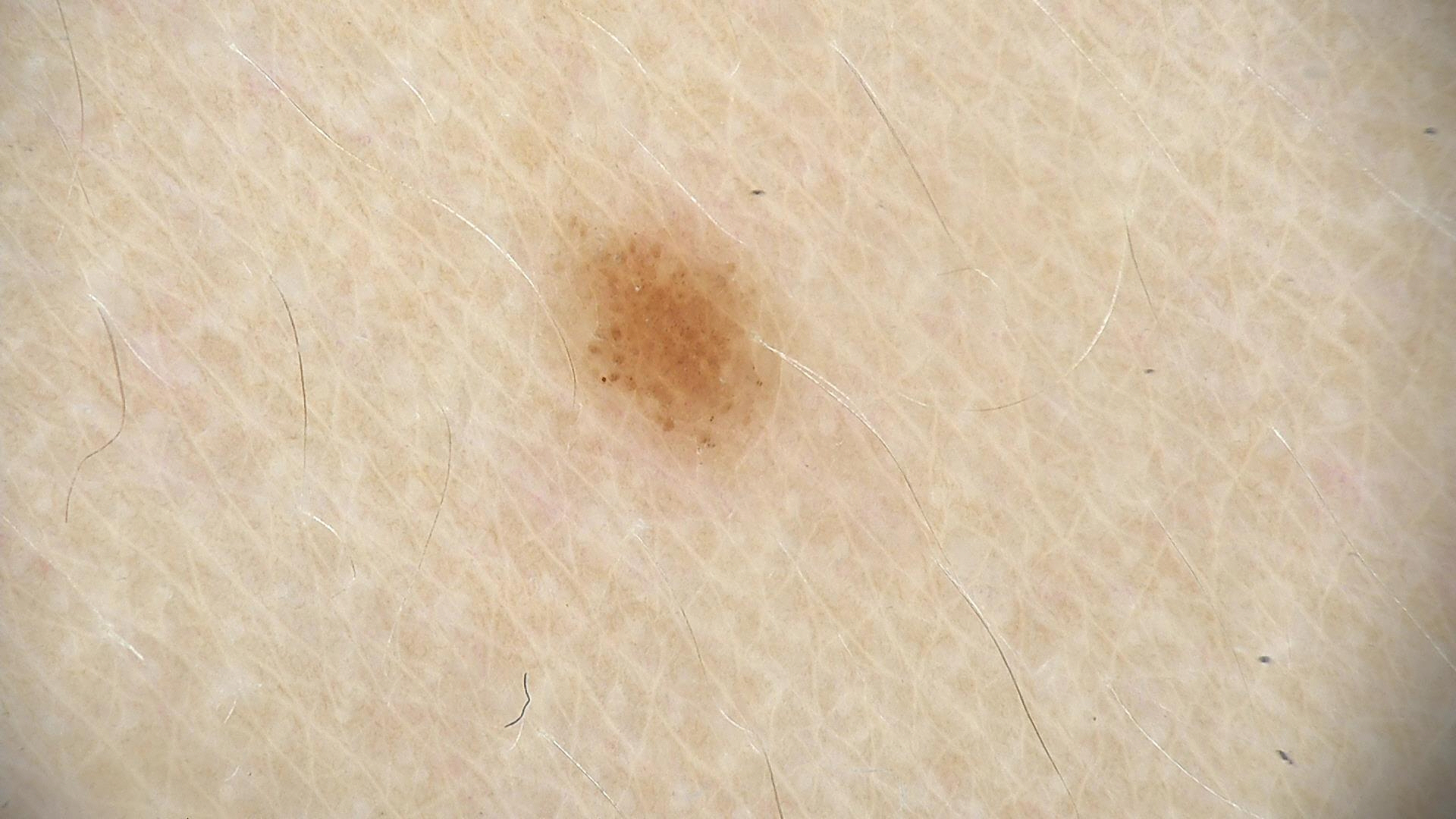A dermoscopic close-up of a skin lesion.
Classified as a benign lesion — a dysplastic junctional nevus.